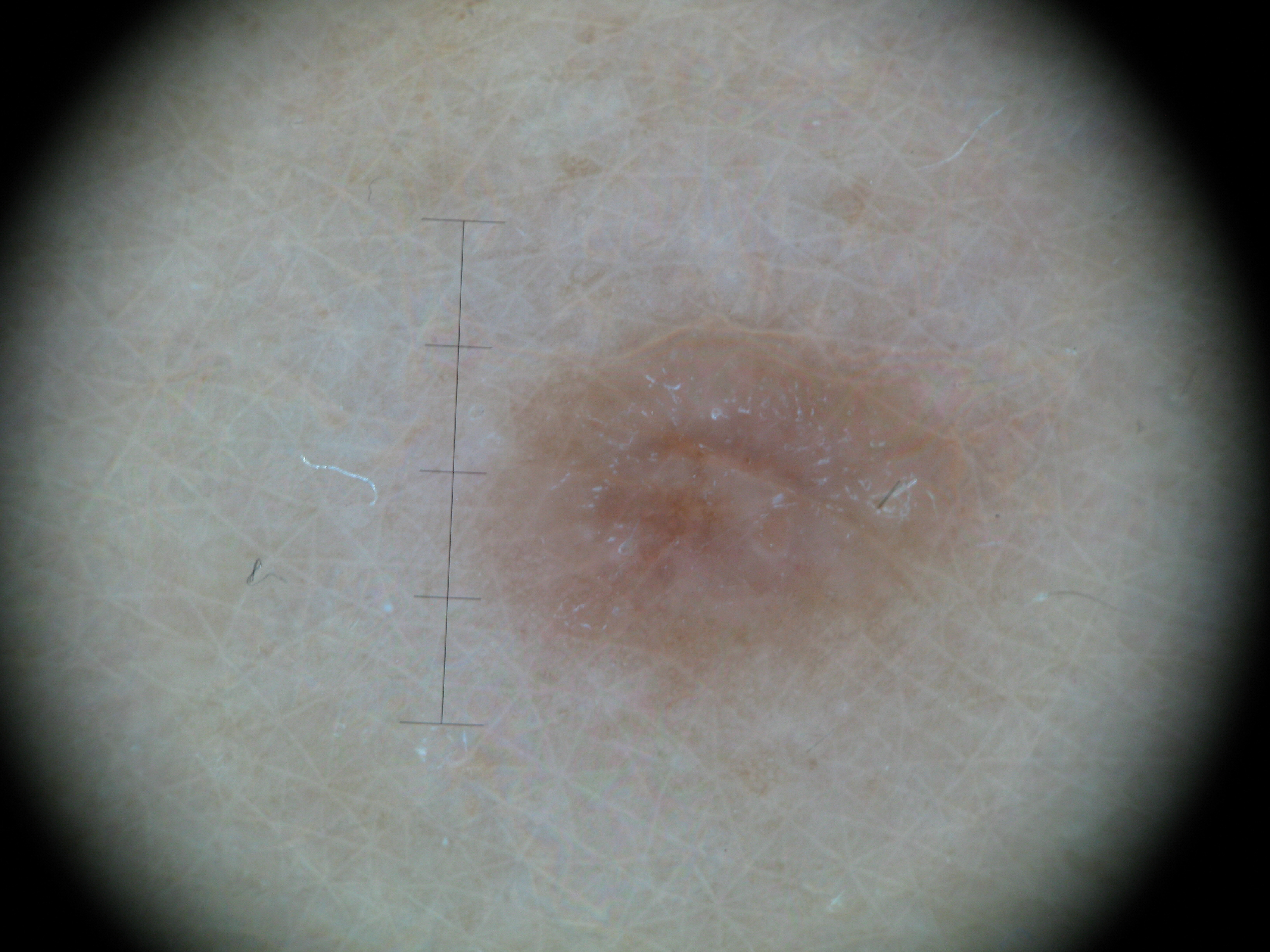- imaging · dermoscopy
- subtype · fibro-histiocytic
- assessment · dermatofibroma (expert consensus)